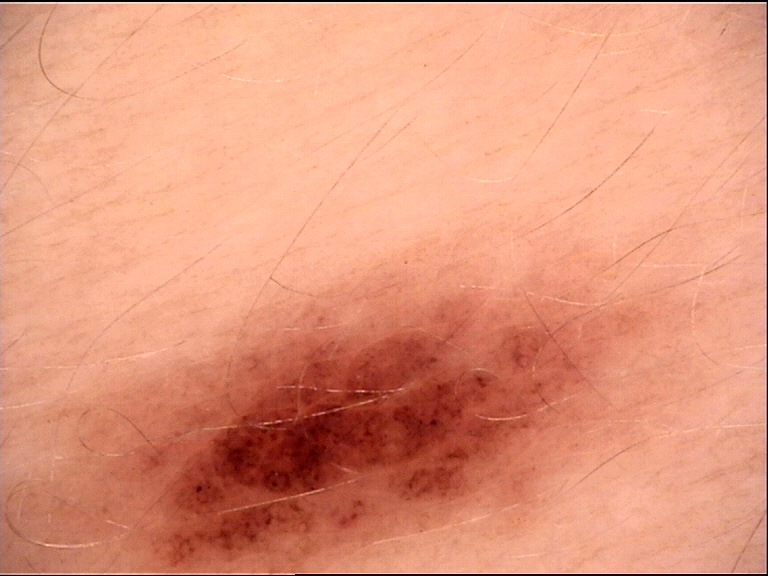Q: What is this lesion?
A: dysplastic junctional nevus (expert consensus)